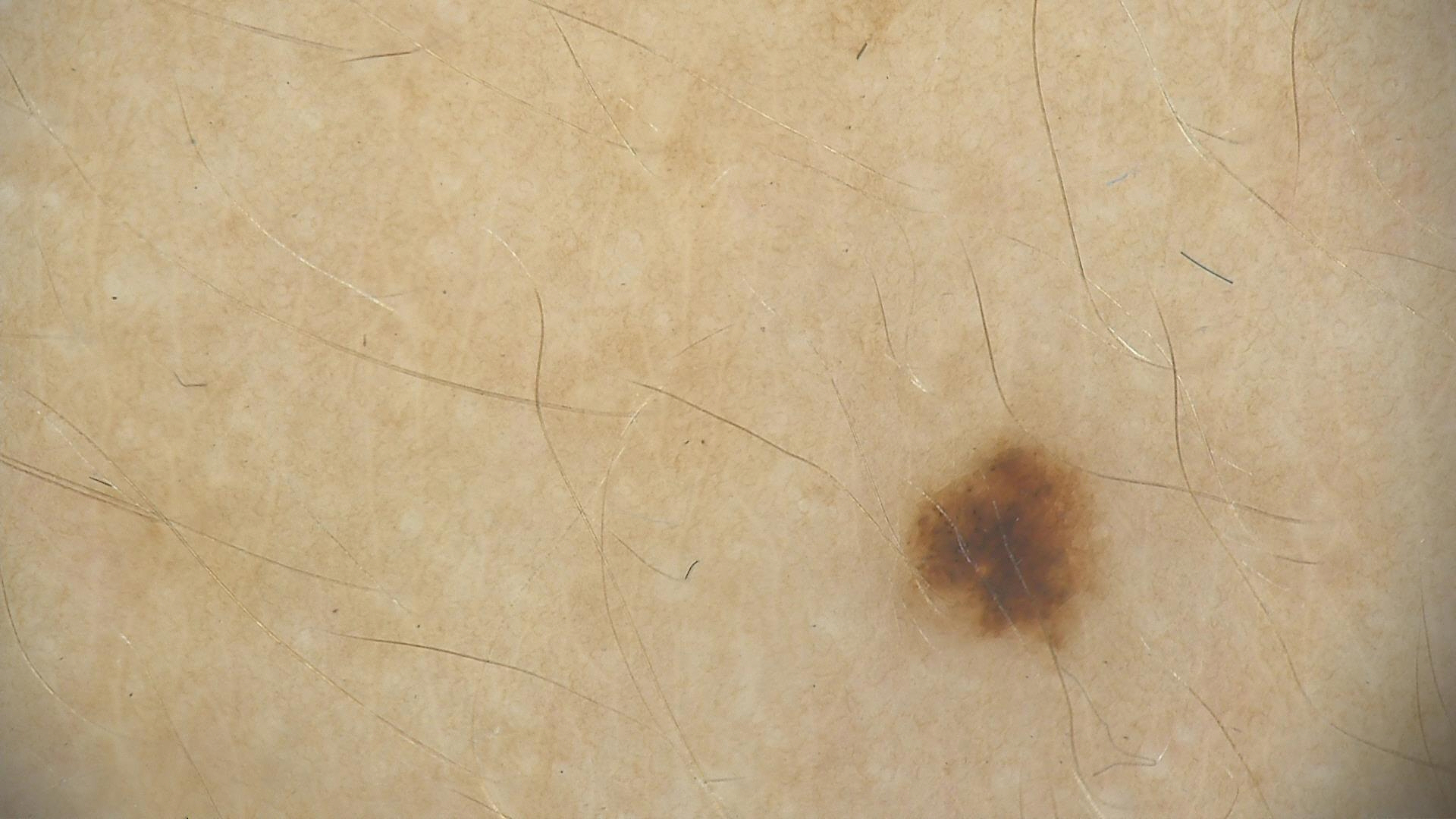The diagnosis was a dysplastic junctional nevus.